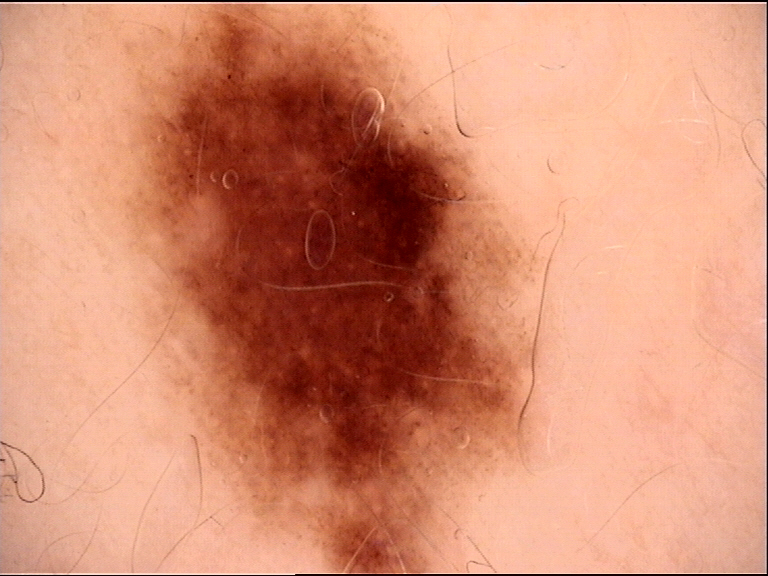A dermoscopic close-up of a skin lesion. Classified as a dysplastic junctional nevus.